The photo was captured at a distance, located on the front of the torso — 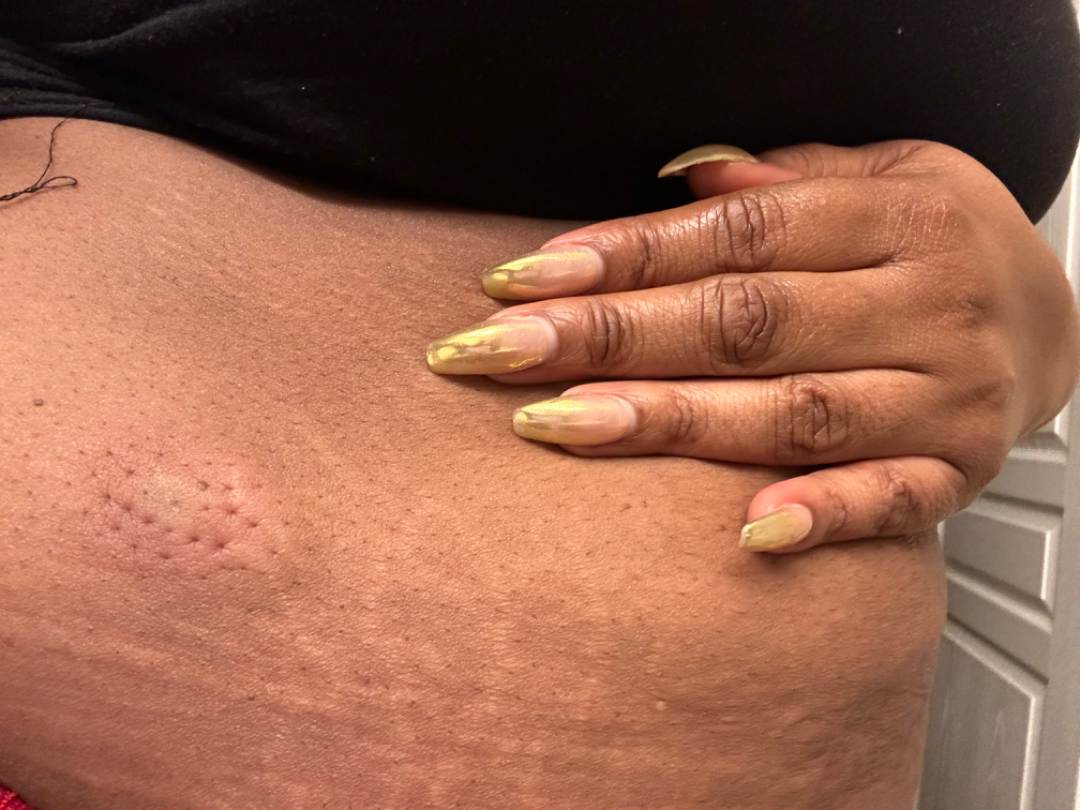Q: What conditions are considered?
A: most consistent with Insect Bite